Dermoscopy of a skin lesion · a female subject roughly 40 years of age — 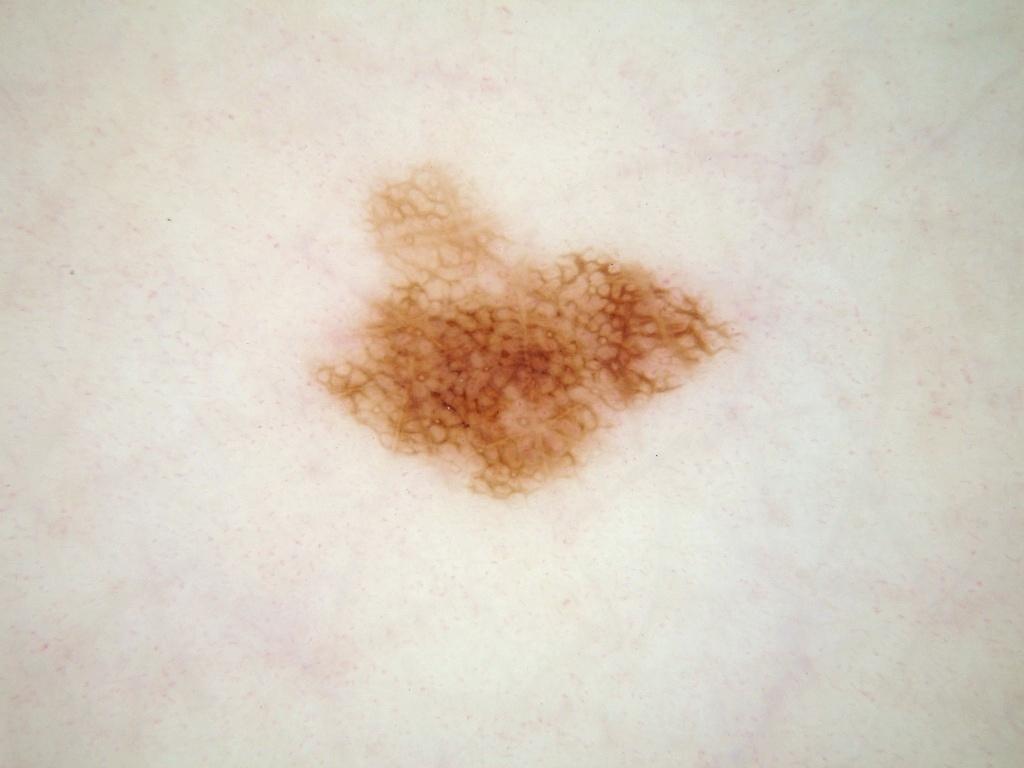Image and clinical context:
A mid-sized lesion within the field. With coordinates (x1, y1, x2, y2), the lesion is located at bbox=[303, 158, 751, 503]. The dermoscopic pattern shows globules and pigment network.
Assessment:
The clinical diagnosis was a melanocytic nevus, a benign skin lesion.